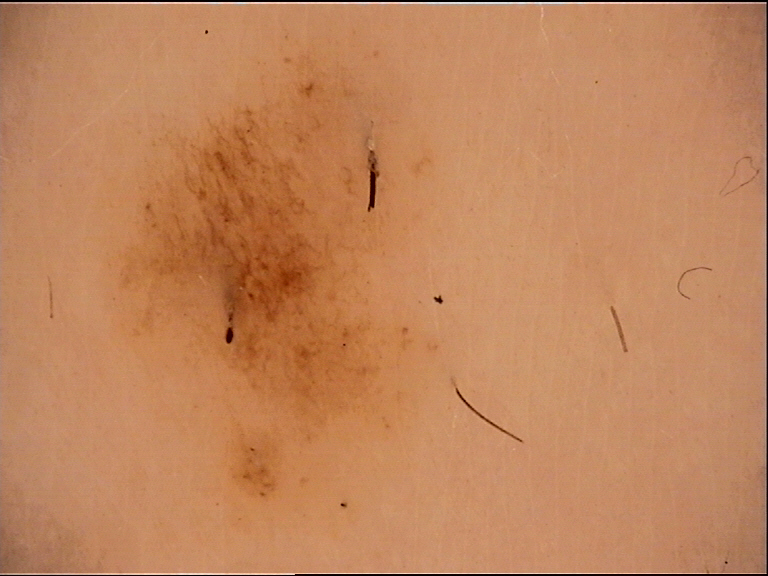Classified as a dysplastic junctional nevus.